A dermoscopic image of a skin lesion; a male patient in their mid-60s — 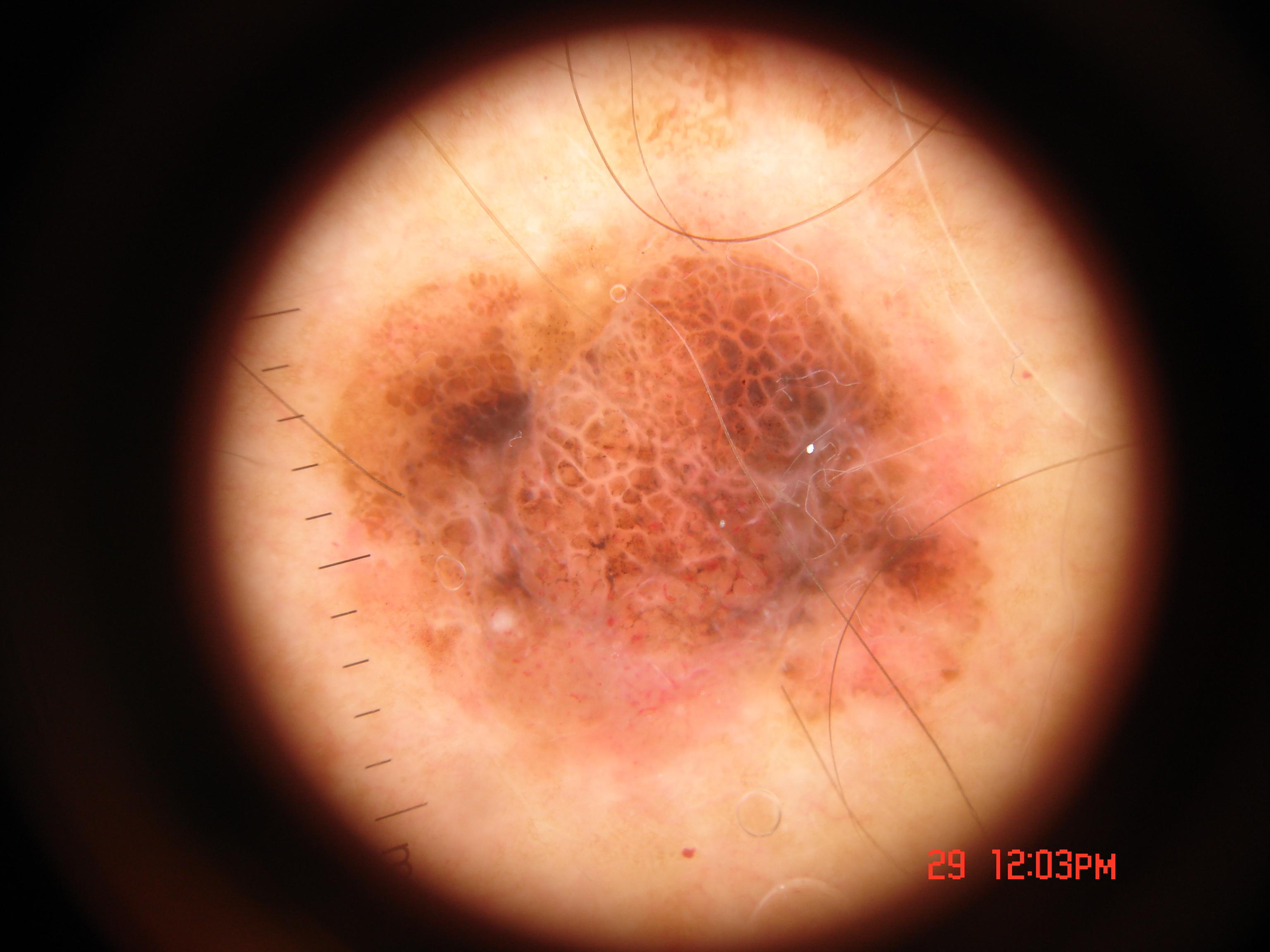Q: Where is the lesion located?
A: (323, 223, 999, 786)
Q: What dermoscopic features are present?
A: globules and negative network; absent: milia-like cysts, pigment network, and streaks
Q: Lesion extent?
A: moderate
Q: What is this lesion?
A: a melanoma